A dermoscopic close-up of a skin lesion.
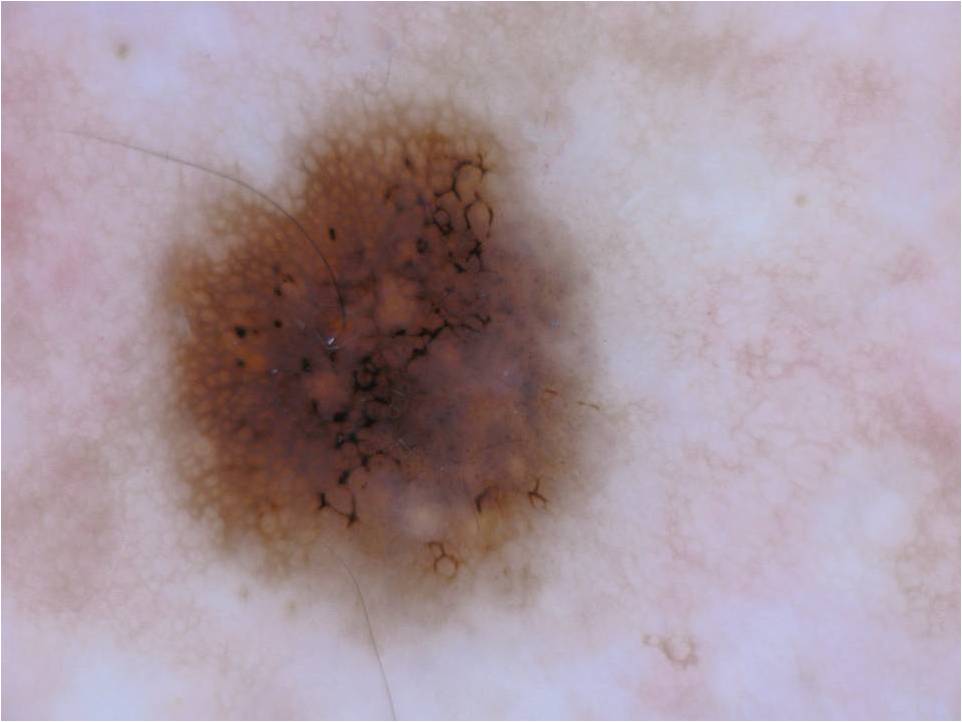Case summary:
A mid-sized lesion within the field. In (x1, y1, x2, y2) order, the visible lesion spans <box>125, 86, 606, 629</box>. Dermoscopy demonstrates pigment network, milia-like cysts, and globules.
Assessment:
Consistent with a melanocytic nevus.